Acquired for a research image collection, with no referral diagnosis; a female subject 73 years old — 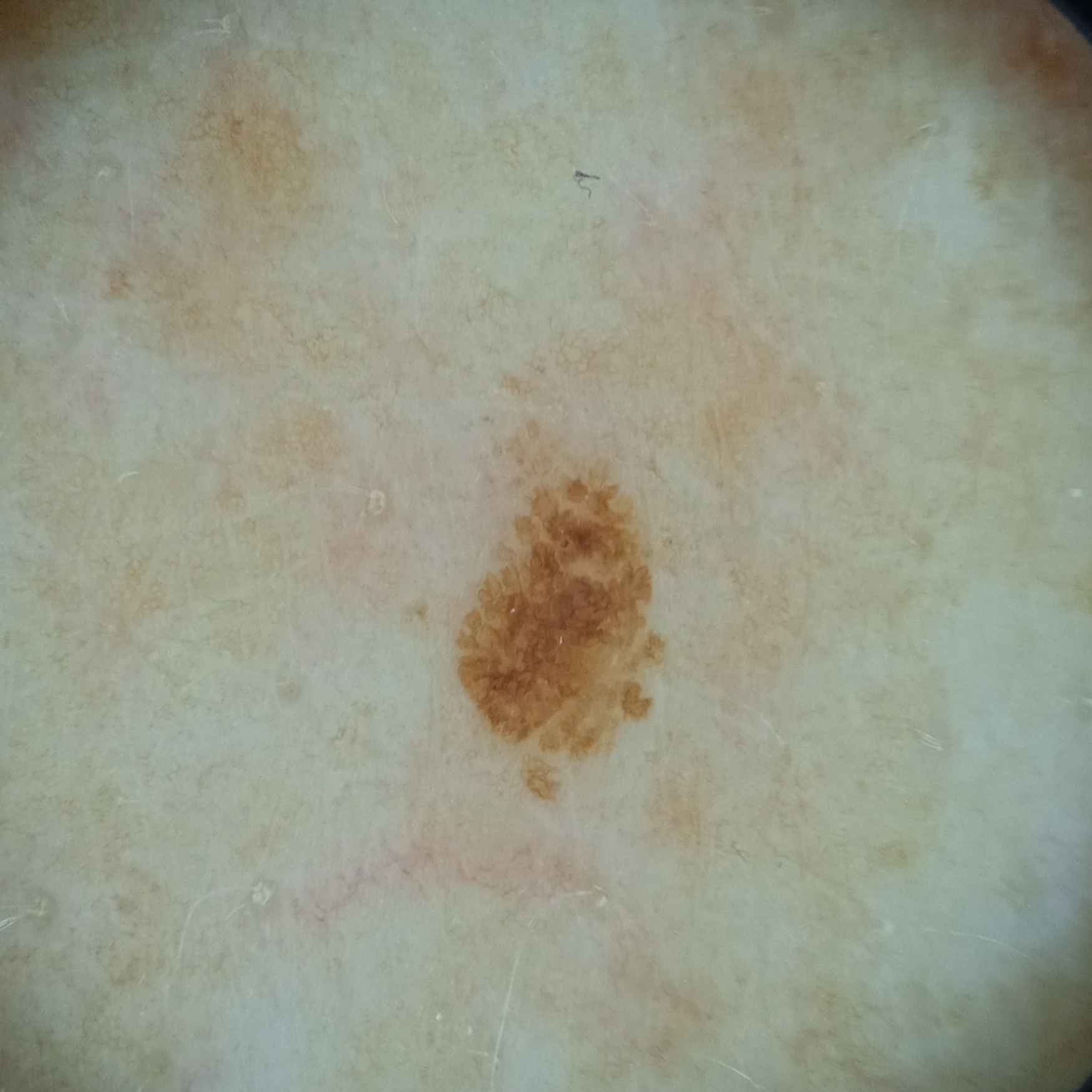- anatomic site: the back
- diameter: 3.9 mm
- diagnosis: seborrheic keratosis (dermatologist consensus)